A subject in their mid-50s:
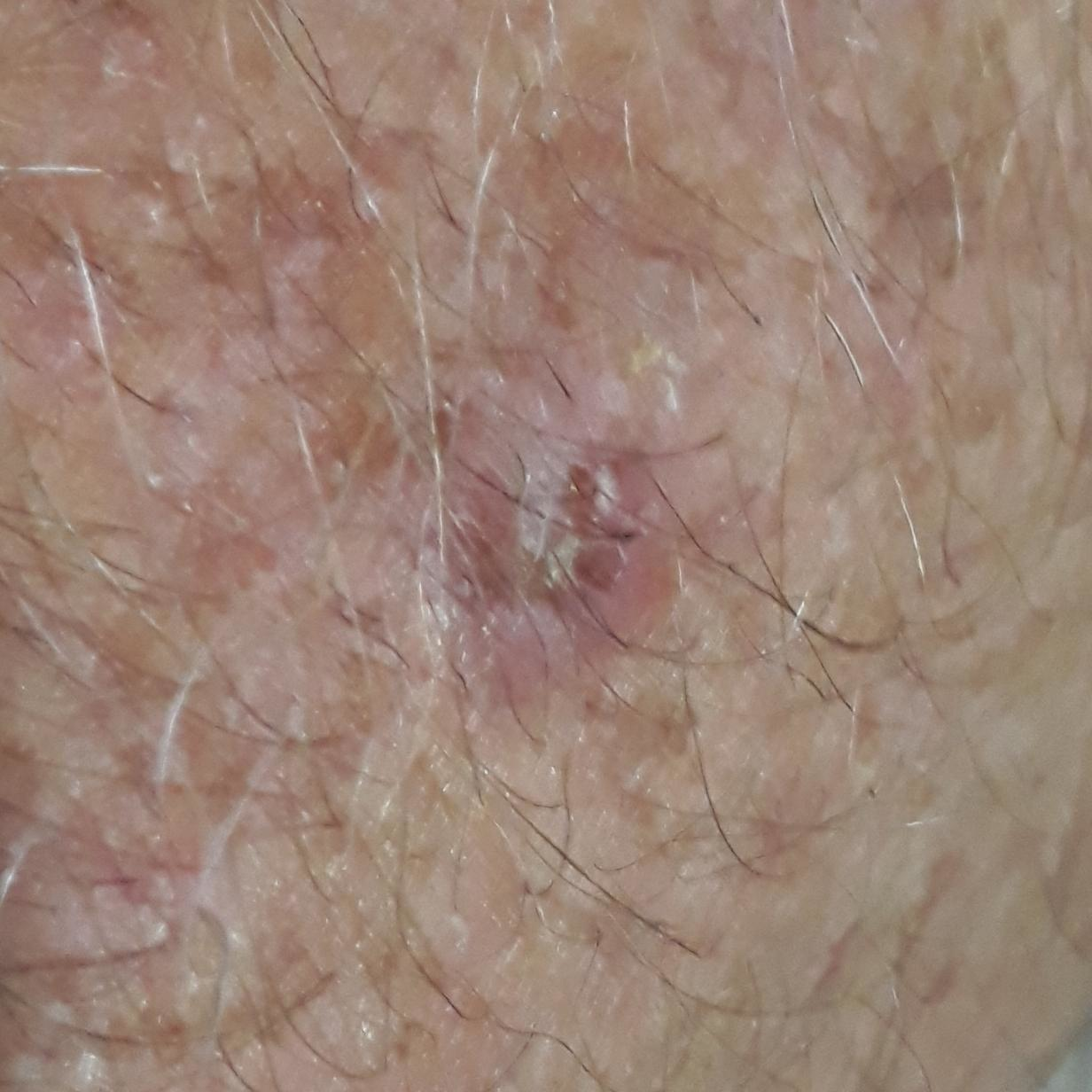Located on a forearm. By the patient's account, the lesion itches. Consistent with an actinic keratosis.